A male patient 44 years old; a clinical photograph showing a skin lesion — 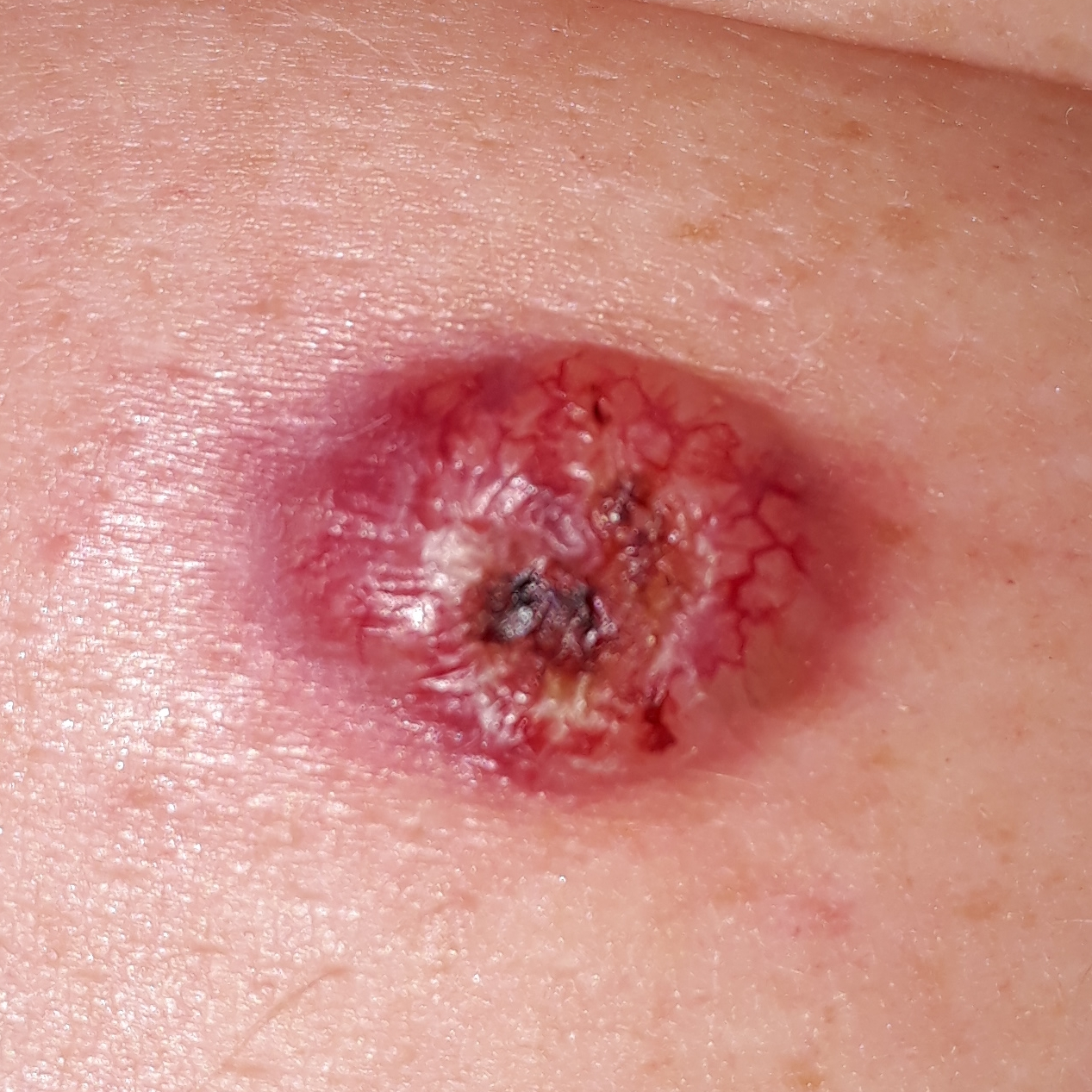Summary: The lesion was found on the abdomen. Per patient report, the lesion itches, has bled, is elevated, and hurts. Pathology: The biopsy diagnosis was a basal cell carcinoma.